A clinical photograph of a skin lesion · recorded as skin type II · a male subject aged around 85 or older:
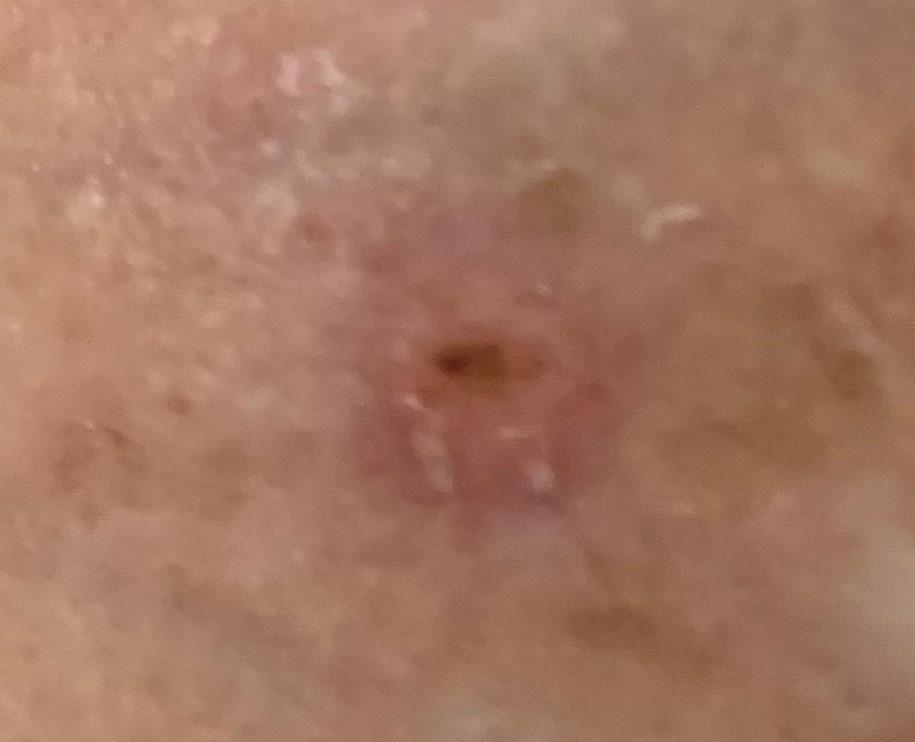location: the head or neck
pathology: Basal cell carcinoma (biopsy-proven)